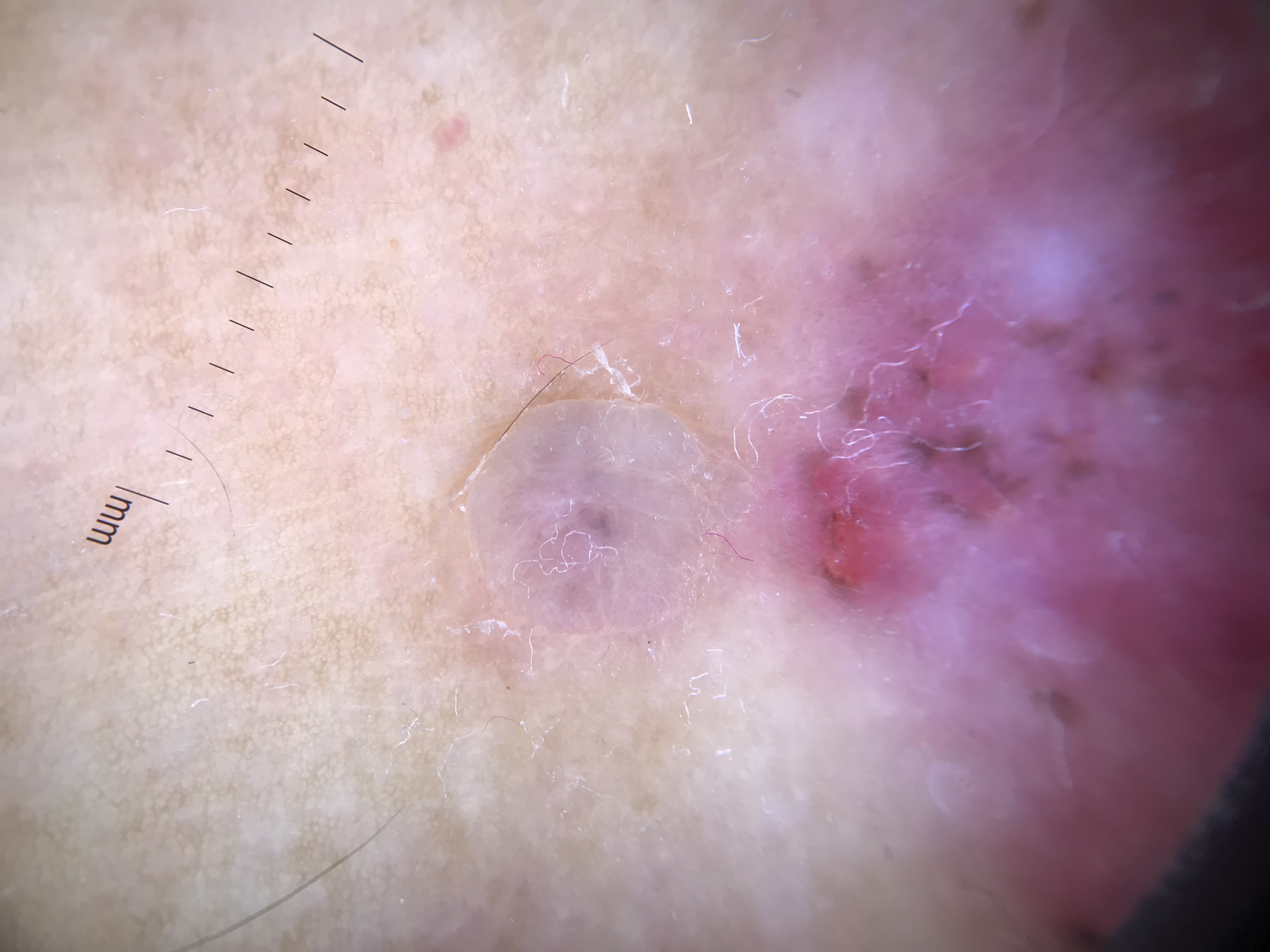A dermoscopic close-up of a skin lesion.
Confirmed on histopathology as a keratinocytic lesion — a basal cell carcinoma.